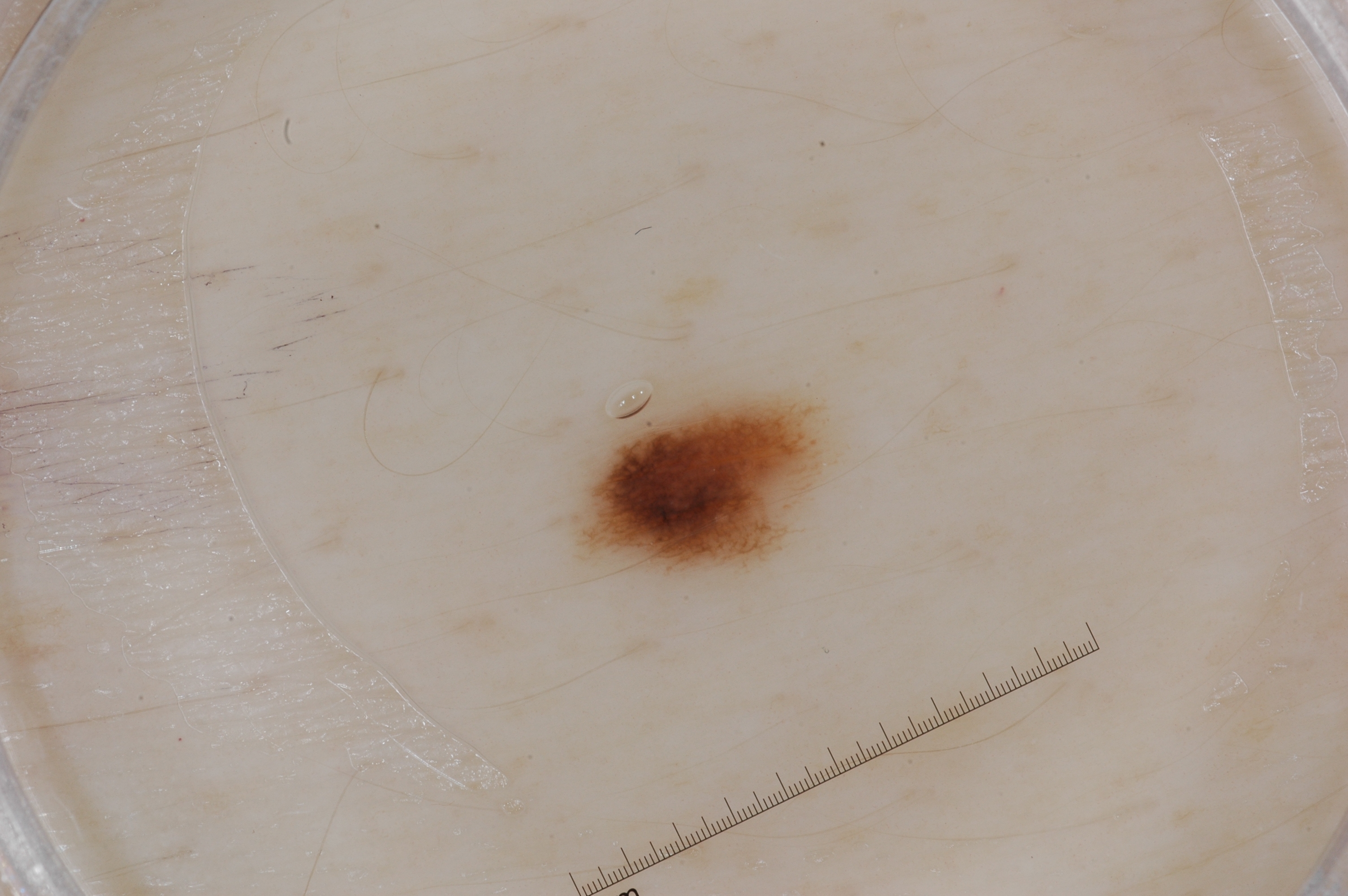Image and clinical context:
A dermoscopic image of a skin lesion. As (left, top, right, bottom), the lesion's extent is 579, 385, 832, 574.
Conclusion:
Expert review diagnosed this as a melanocytic nevus.